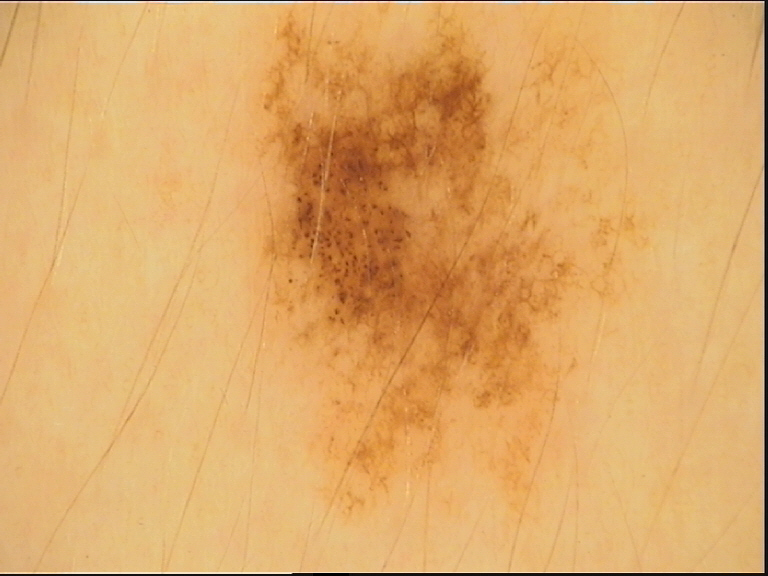modality — dermoscopy
diagnostic label — dysplastic junctional nevus (expert consensus)